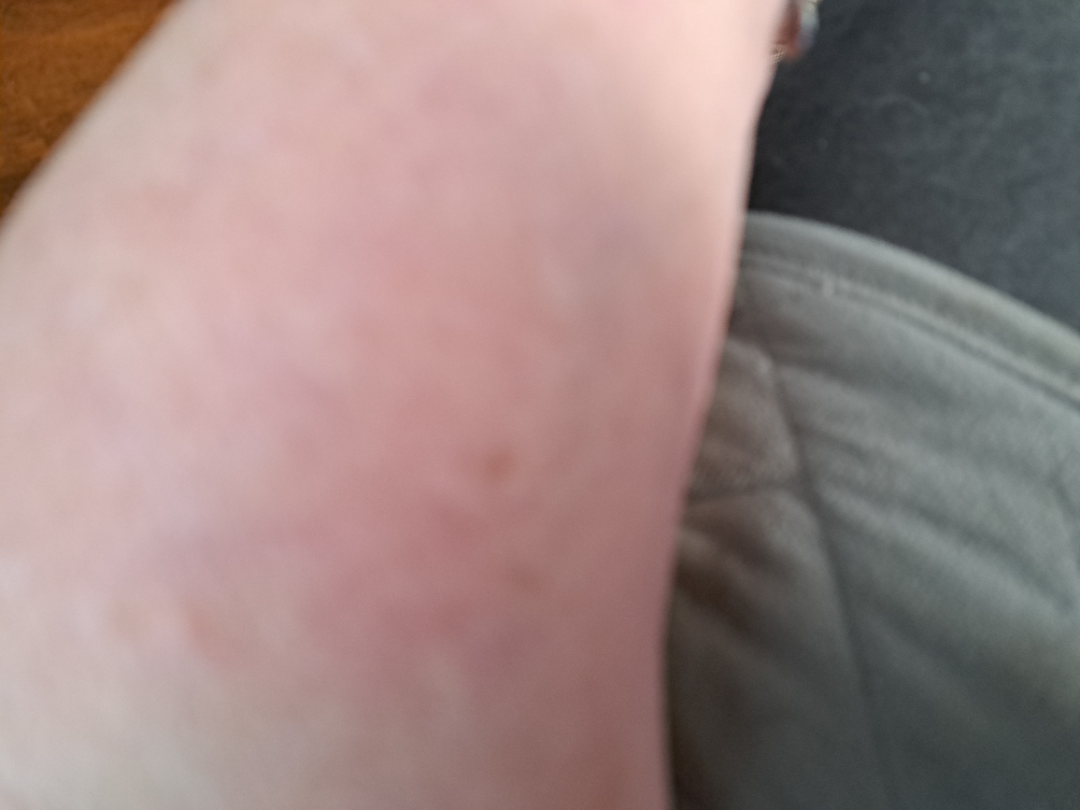- assessment — indeterminate
- subject — female
- symptoms — none reported
- present for — one to four weeks
- surface texture — flat
- image framing — close-up